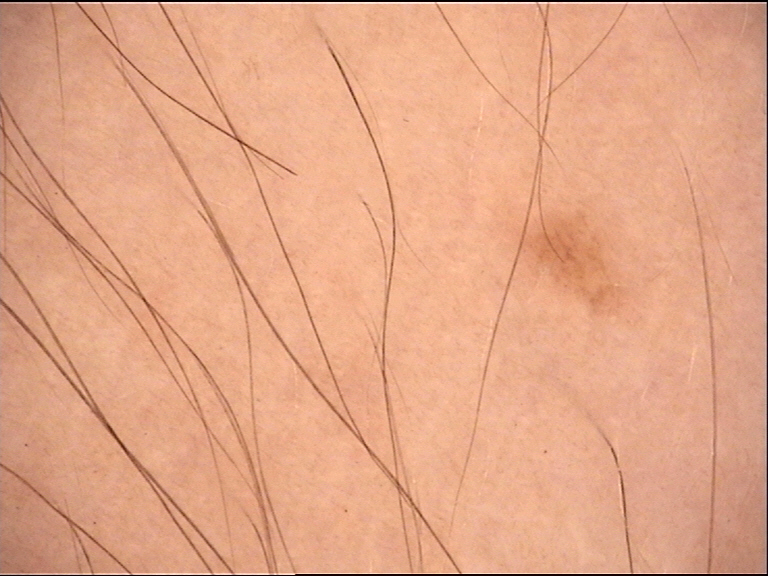| key | value |
|---|---|
| imaging | dermoscopy |
| class | dysplastic junctional nevus (expert consensus) |